This image was taken at a distance. The patient is 30–39, male:
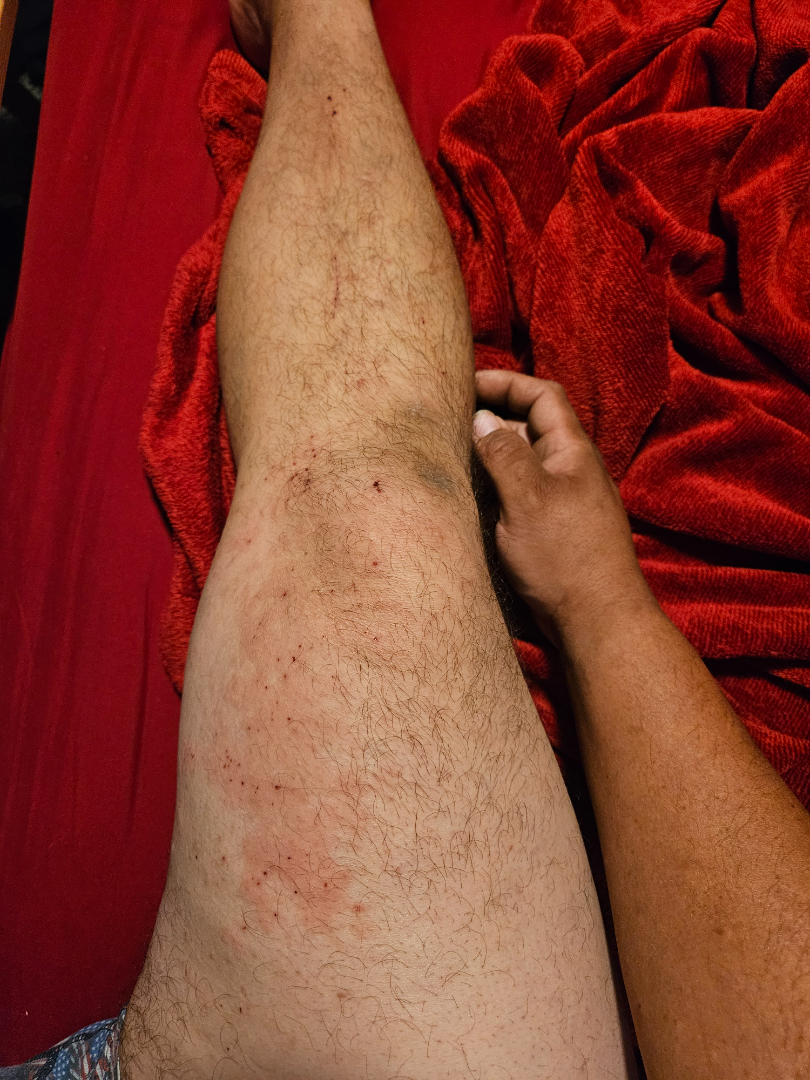The impression on review was Acute and chronic dermatitis.